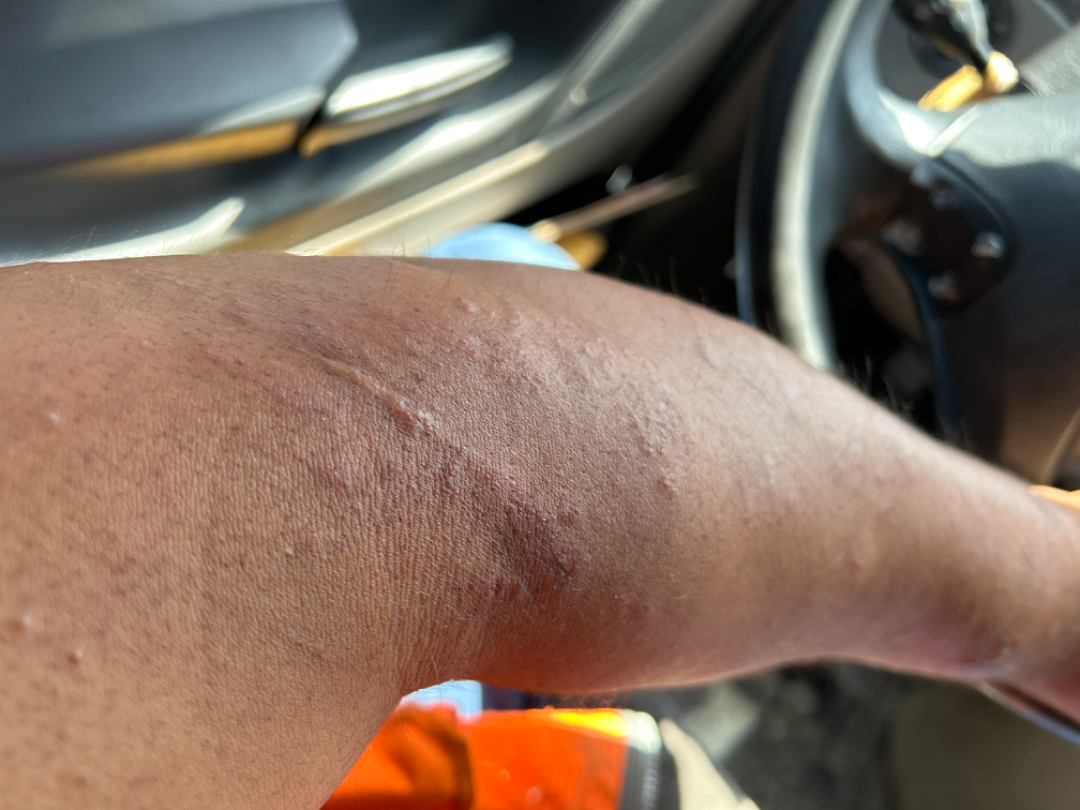Notes:
* contributor · male, age 40–49
* framing · at an angle
* site · arm
* assessment · three independent reviewers: the favored diagnosis is Allergic Contact Dermatitis; lower on the differential is Acute dermatitis, NOS; less probable is Deep fungal infection; less likely is Abscess; a more distant consideration is Eczema